The photograph is a close-up of the affected area, reported duration is less than one week, the contributor notes the lesion is raised or bumpy, the front of the torso is involved, the patient considered this a rash, skin tone: FST III; lay graders estimated Monk Skin Tone 2–3, symptoms reported: pain and itching:
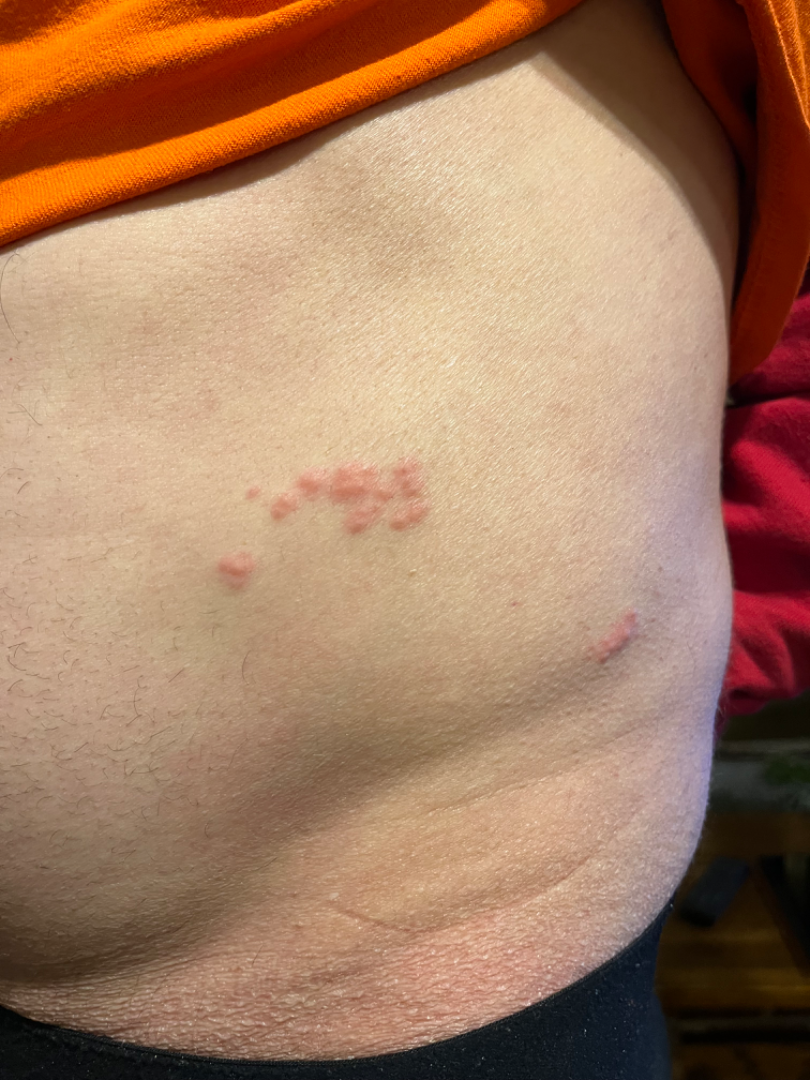{
  "differential": {
    "leading": [
      "Herpes Zoster"
    ],
    "considered": [
      "Allergic Contact Dermatitis"
    ]
  }
}